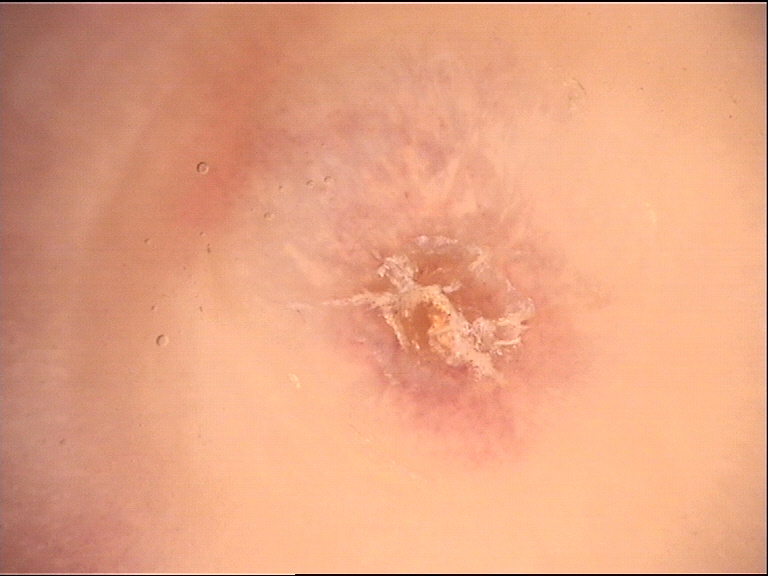Diagnosed as a fibro-histiocytic lesion — a dermatofibroma.